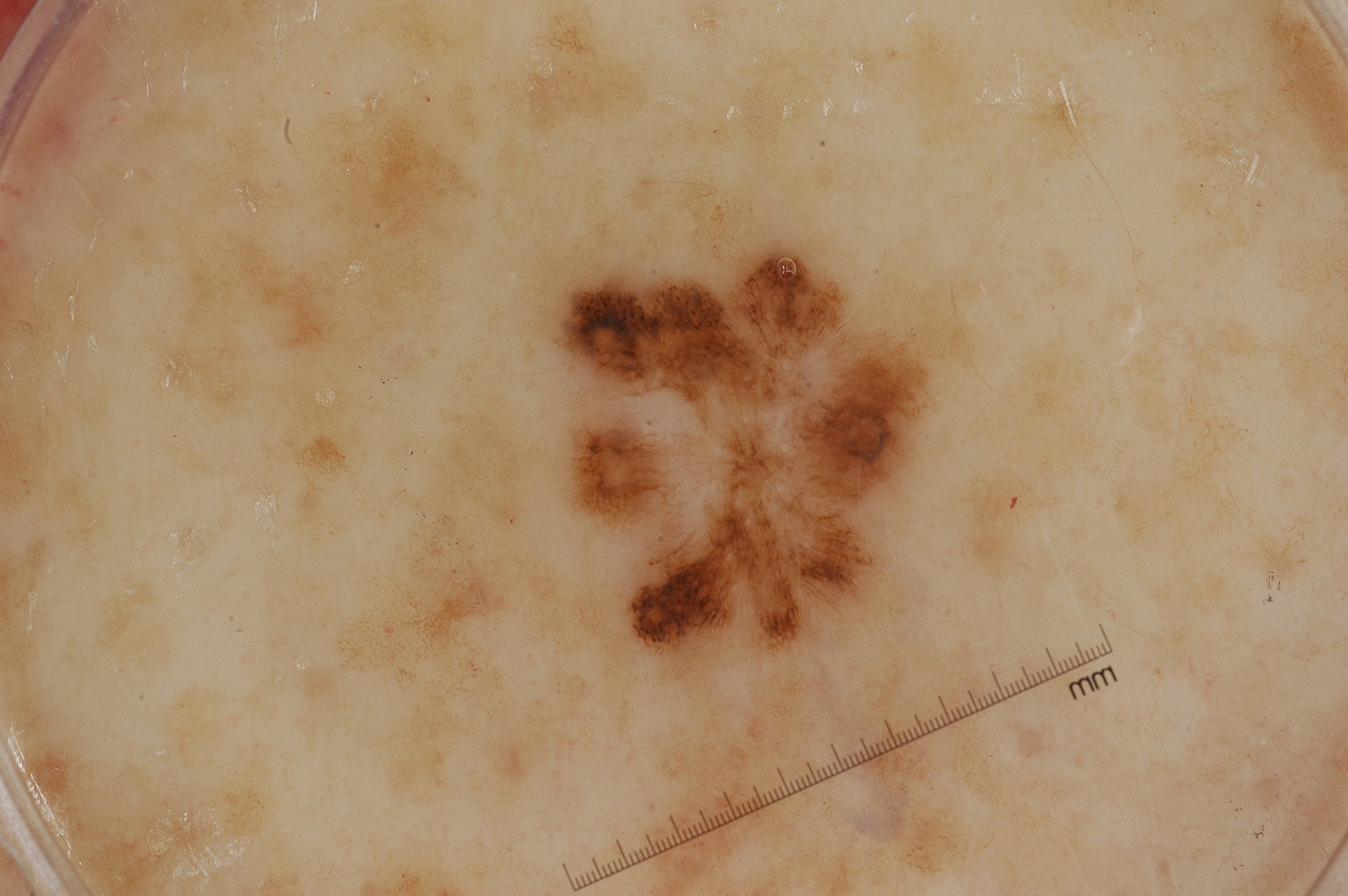Case summary:
A female subject in their 60s. A dermoscopic close-up of a skin lesion. With coordinates (x1, y1, x2, y2), the lesion's extent is [548, 231, 958, 665]. Dermoscopic examination shows pigment network.
Impression:
Clinically diagnosed as a melanocytic nevus.